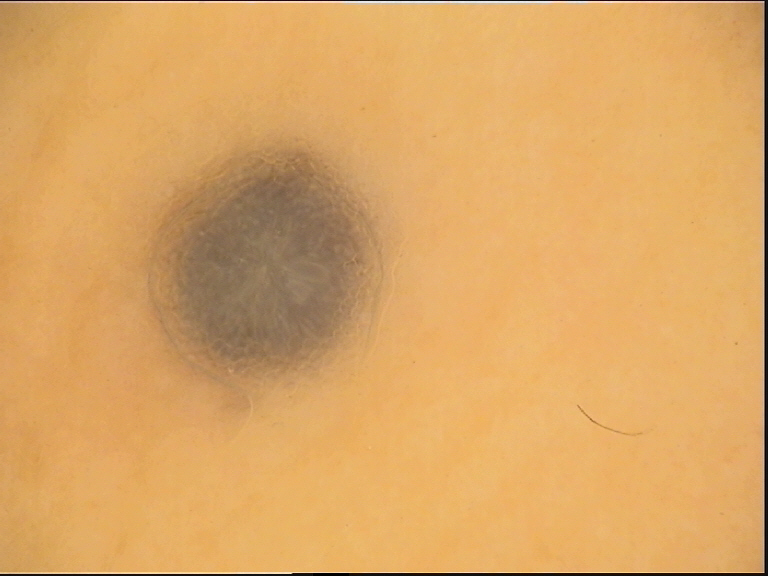class: blue nevus (expert consensus).